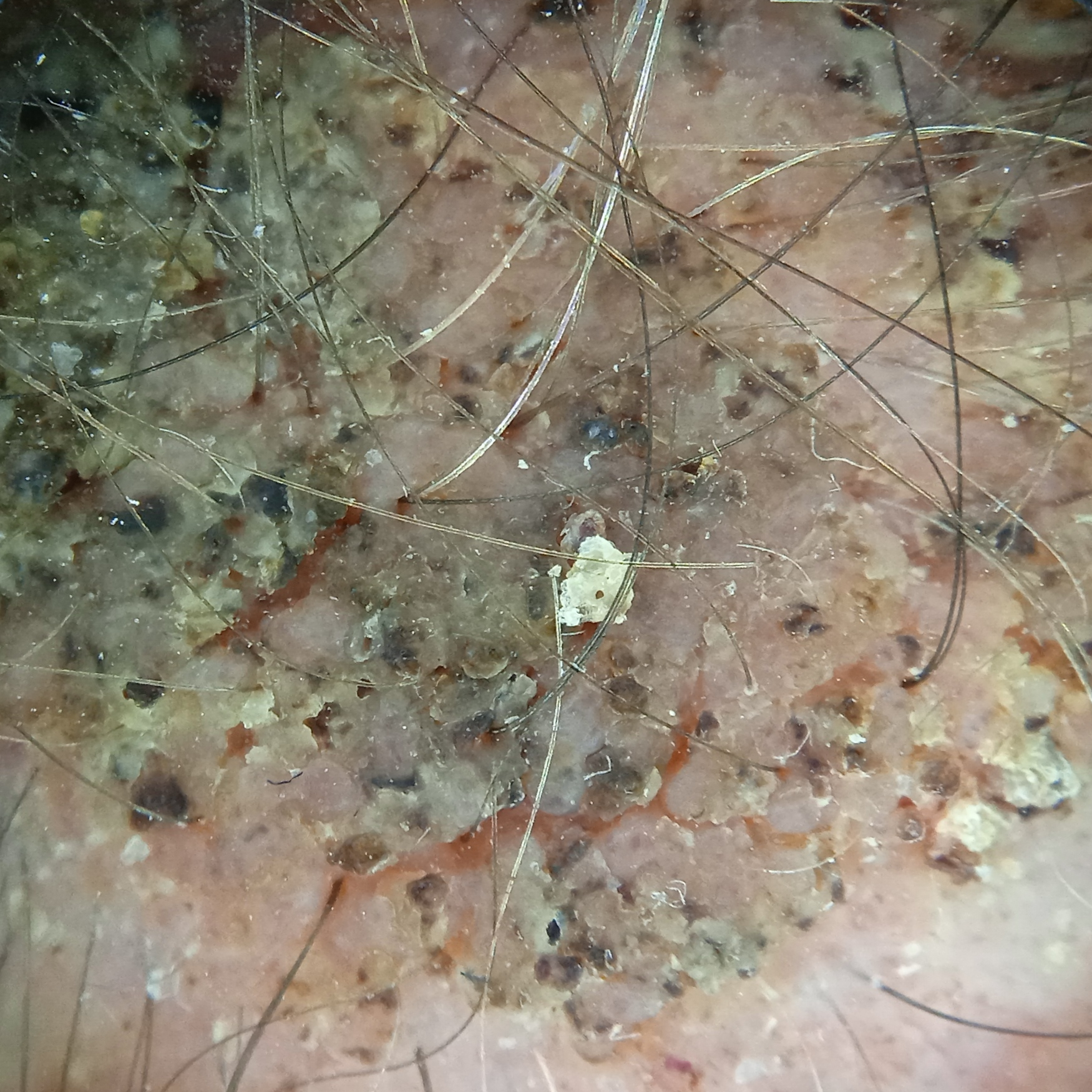<record>
  <mole_burden>a moderate number of melanocytic nevi</mole_burden>
  <image>dermatoscopic image</image>
  <sun_reaction>skin tans without first burning</sun_reaction>
  <lesion_location>the head</lesion_location>
  <diagnosis>
    <name>seborrheic keratosis</name>
    <malignancy>benign</malignancy>
  </diagnosis>
</record>